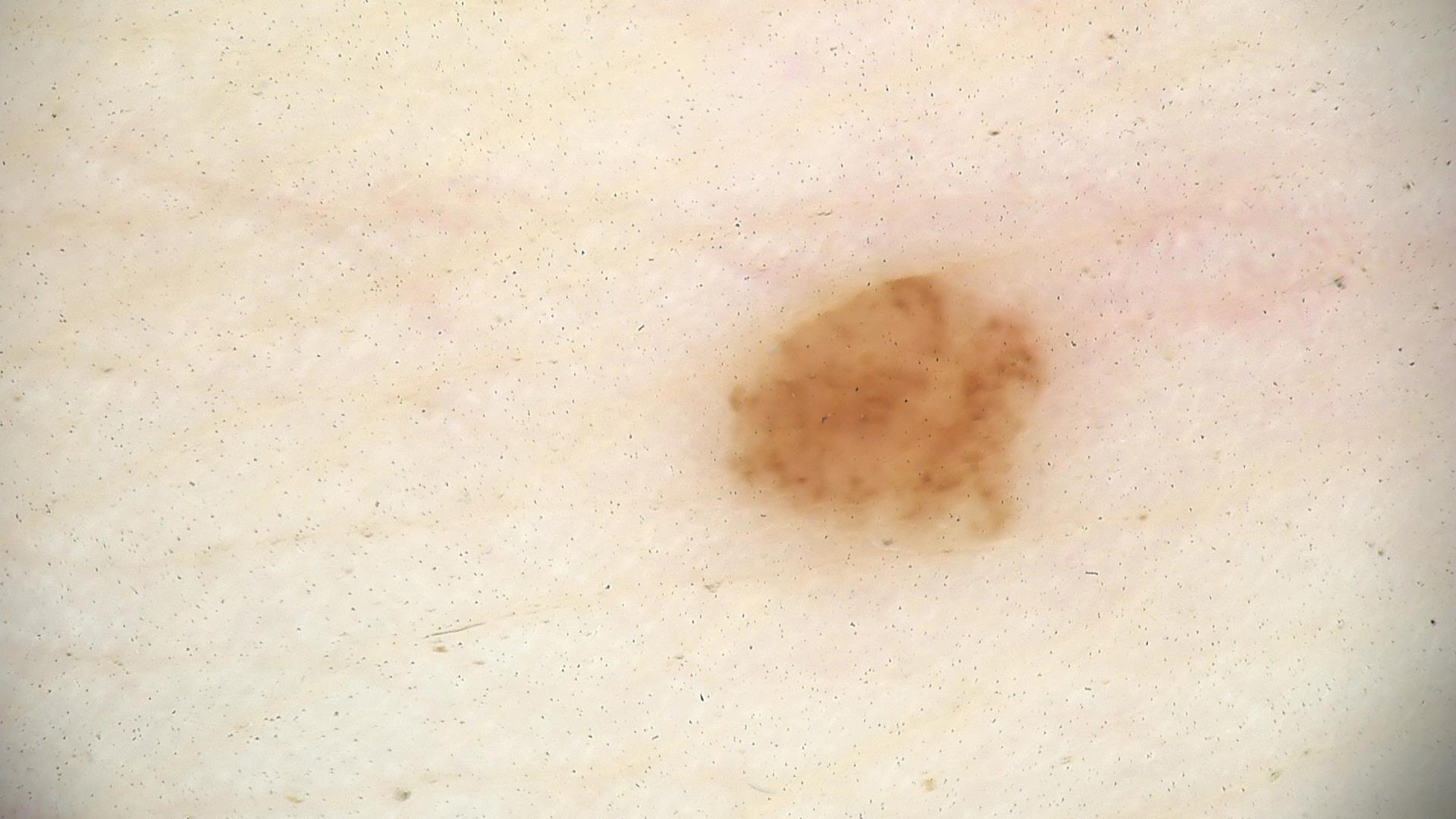Q: What is the imaging modality?
A: dermatoscopy
Q: What was the diagnostic impression?
A: dysplastic junctional nevus (expert consensus)